The patient indicates the lesion is rough or flaky, skin tone: Fitzpatrick skin type IV, the photograph is a close-up of the affected area, the patient is a female aged 50–59: 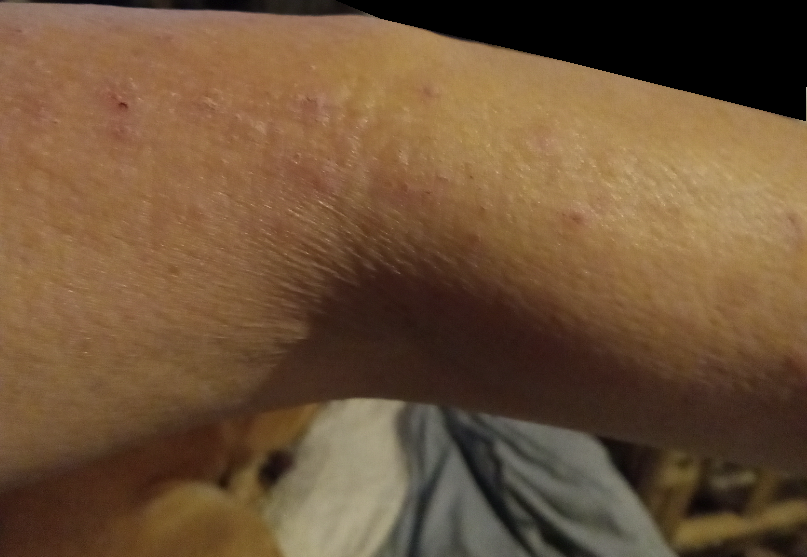Q: What conditions are considered?
A: in keeping with Eczema